This image was taken at a distance:
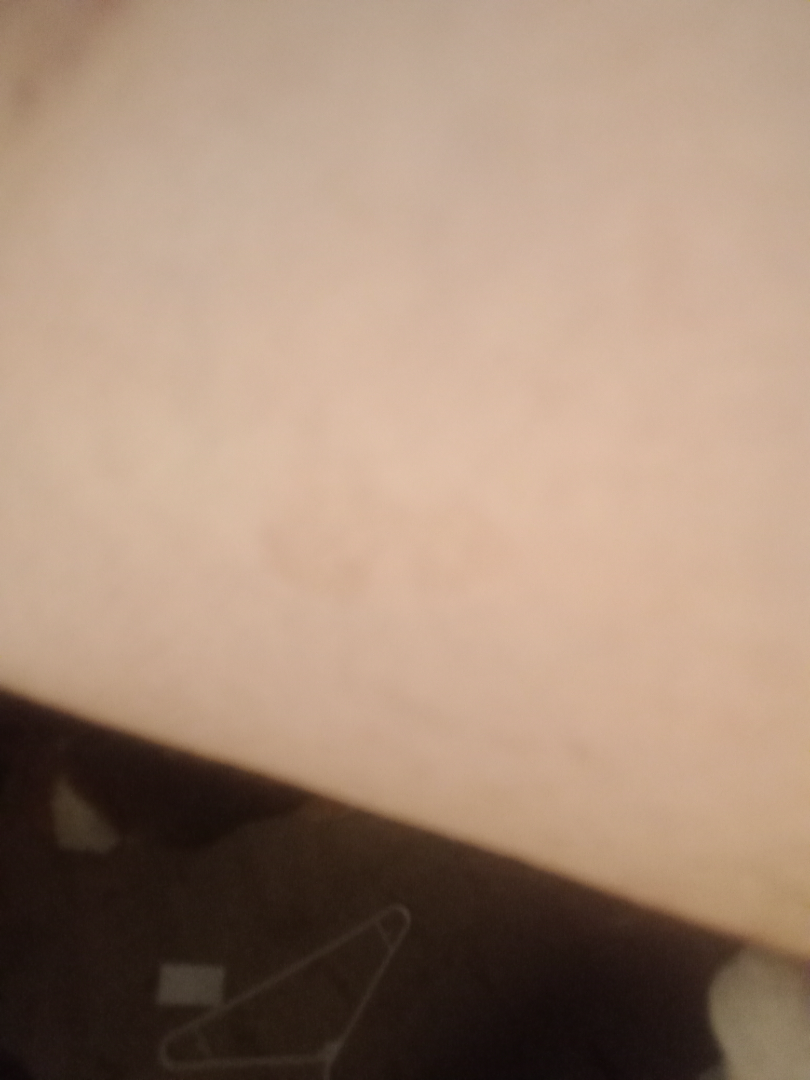Case summary:
• dermatologist impression — favoring Tinea Versicolor; with consideration of Tinea; an alternative is Eczema